The leg is involved · the patient is a male aged 30–39 · close-up view.
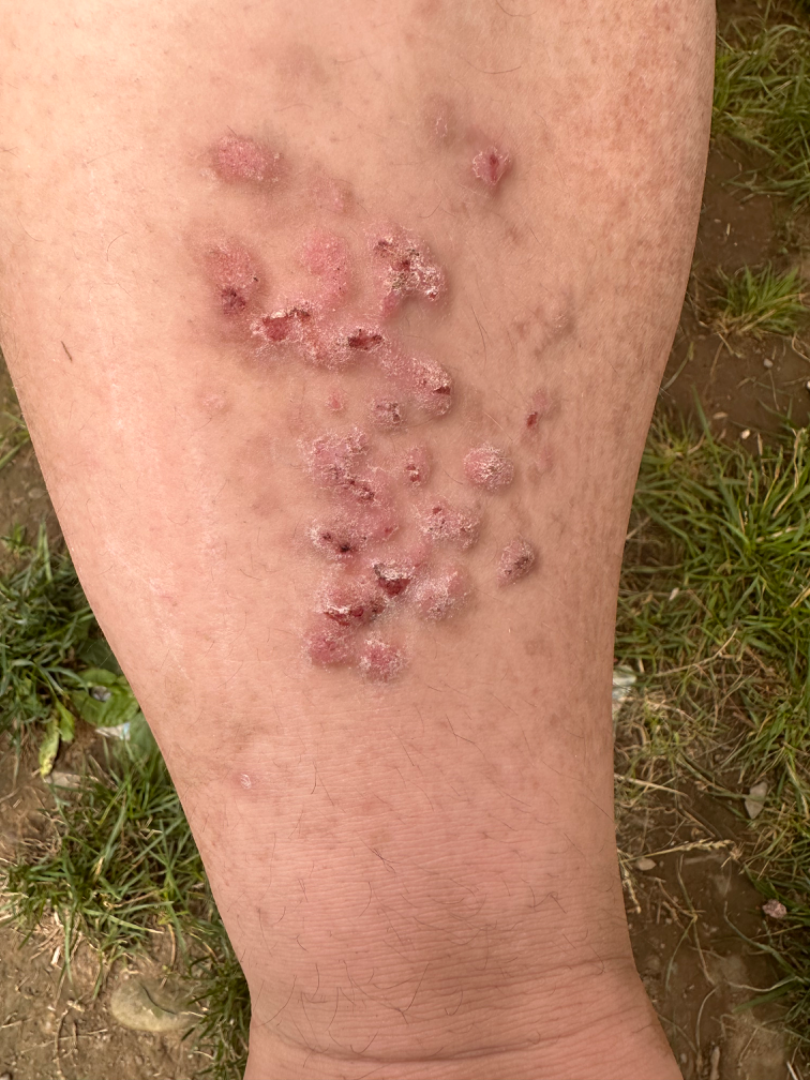History: Present for three to twelve months. The contributor reports the lesion is raised or bumpy. Self-categorized by the patient as skin that appeared healthy to them. No associated systemic symptoms reported. Impression: A single dermatologist reviewed the case: the favored diagnosis is Psoriasis; also on the differential is Prurigo nodularis.